This is a close-up image.
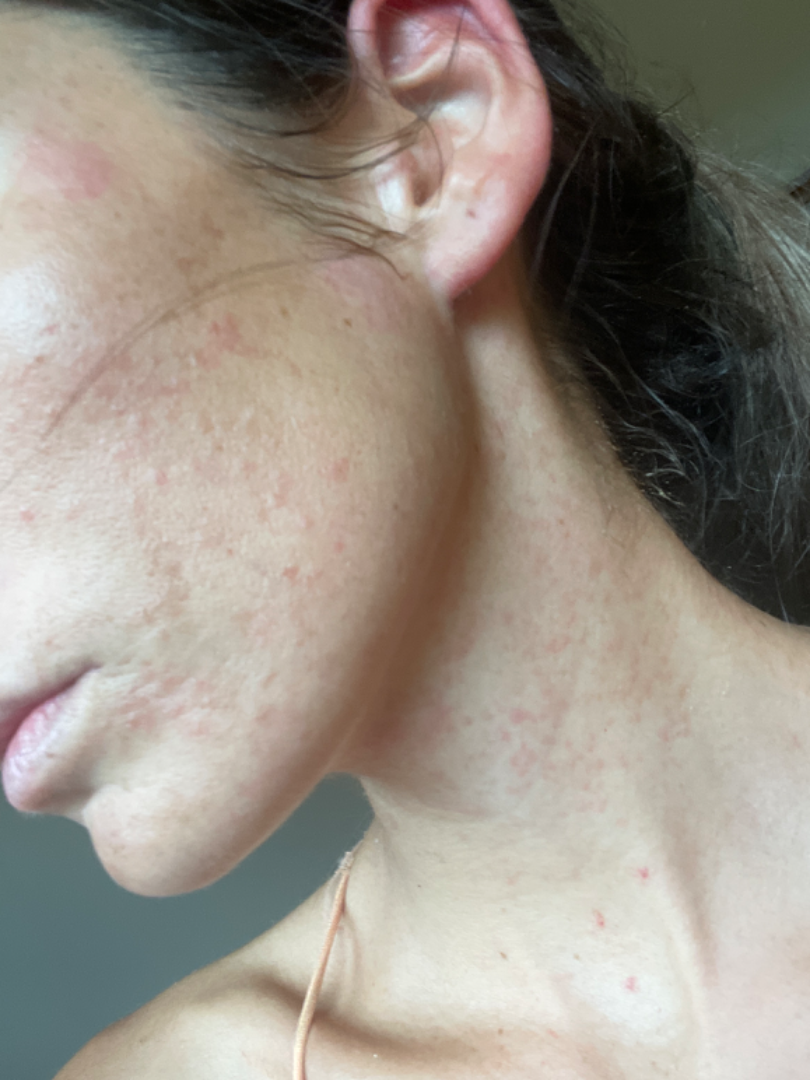Acne (considered); Adnexal neoplasm (considered); Cyst (considered).